This is a dermoscopic photograph of a skin lesion: 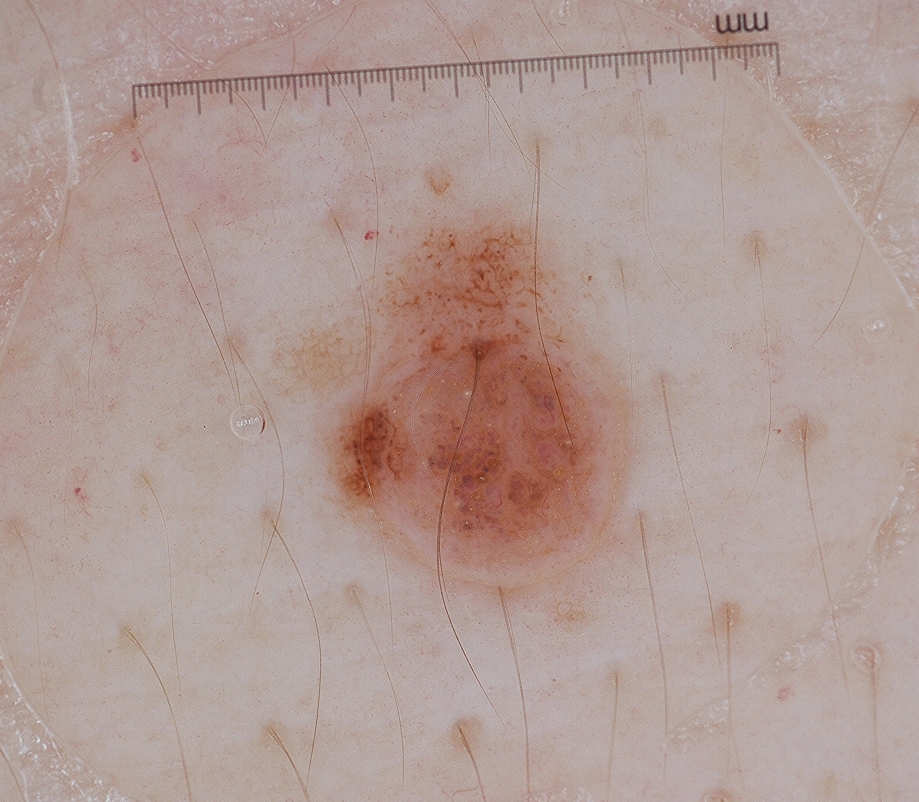dermoscopic pattern = milia-like cysts and globules; bounding box = 267/195/635/590; assessment = a melanocytic nevus, a benign lesion.